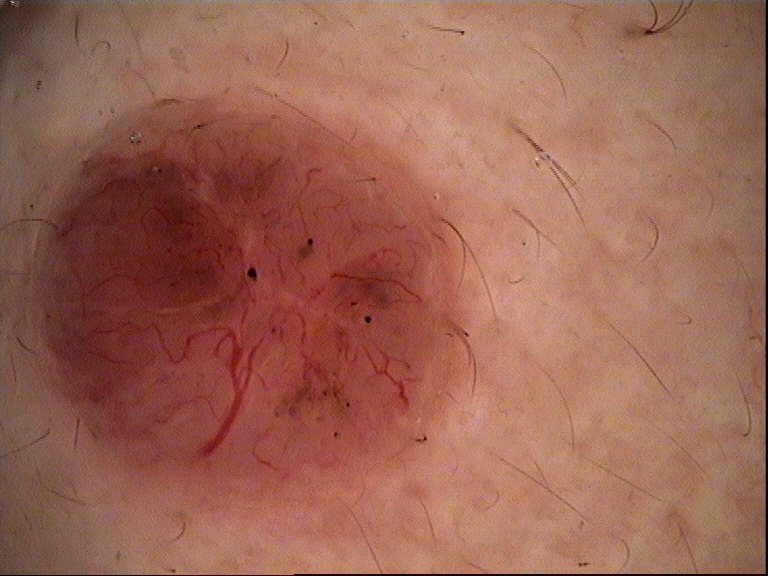A dermoscopic image of a skin lesion.
The biopsy diagnosis was a keratinocytic, malignant lesion — a basal cell carcinoma.